The patient says their skin reddens with sun exposure; collected as part of a research study, without a referral diagnosis; the patient describes having few moles overall; a dermoscopic image of a skin lesion — 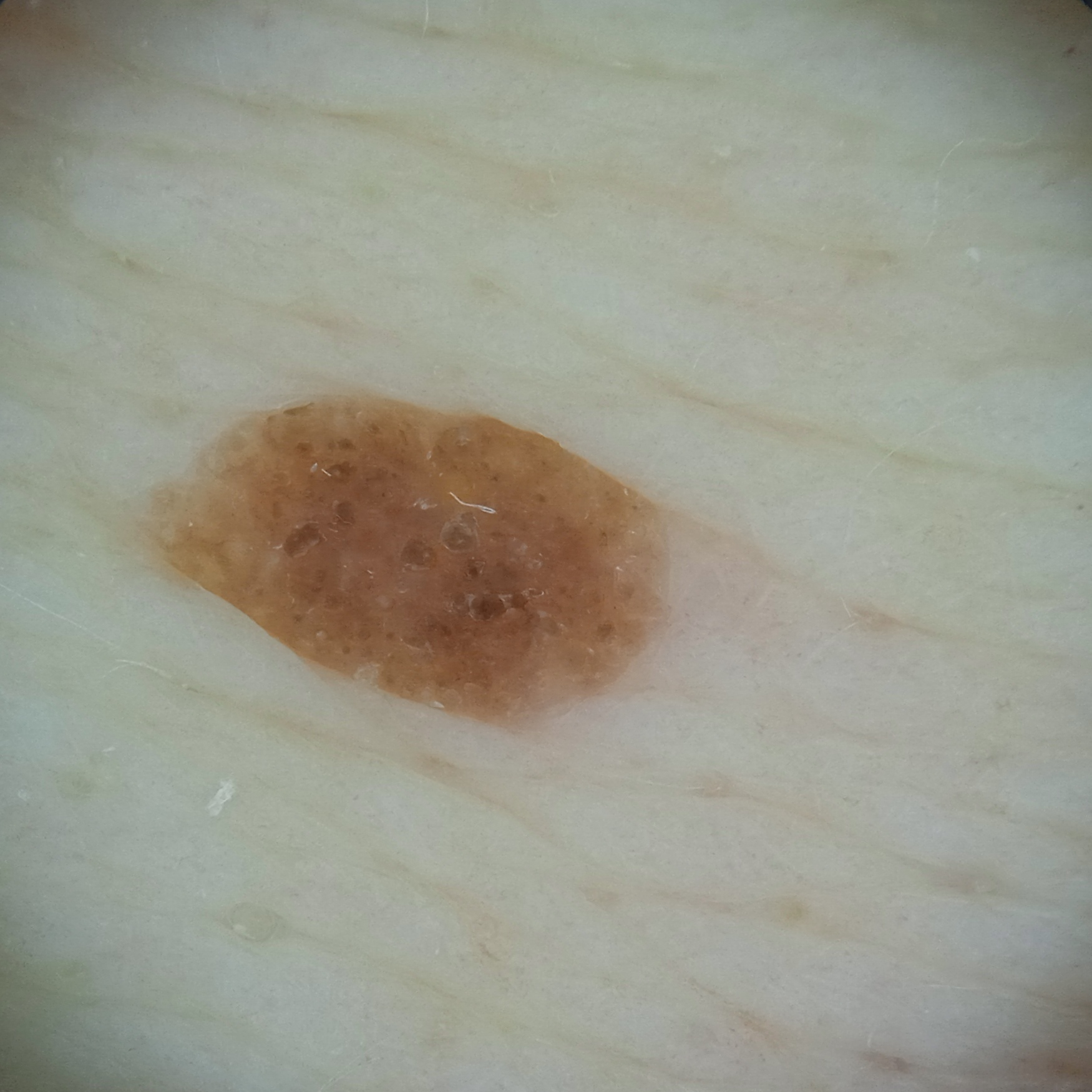{
  "lesion_location": "the back",
  "diagnosis": {
    "name": "seborrheic keratosis",
    "malignancy": "benign"
  }
}